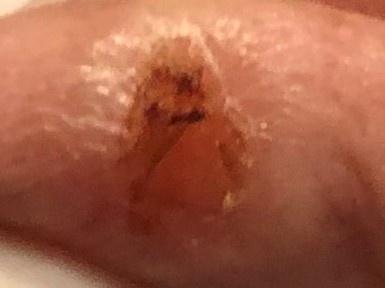A male subject aged around 85 or older.
A clinical photograph showing a skin lesion in context.
The lesion involves the head or neck.
On biopsy, the diagnosis was a malignant, adnexal lesion — a basal cell carcinoma.